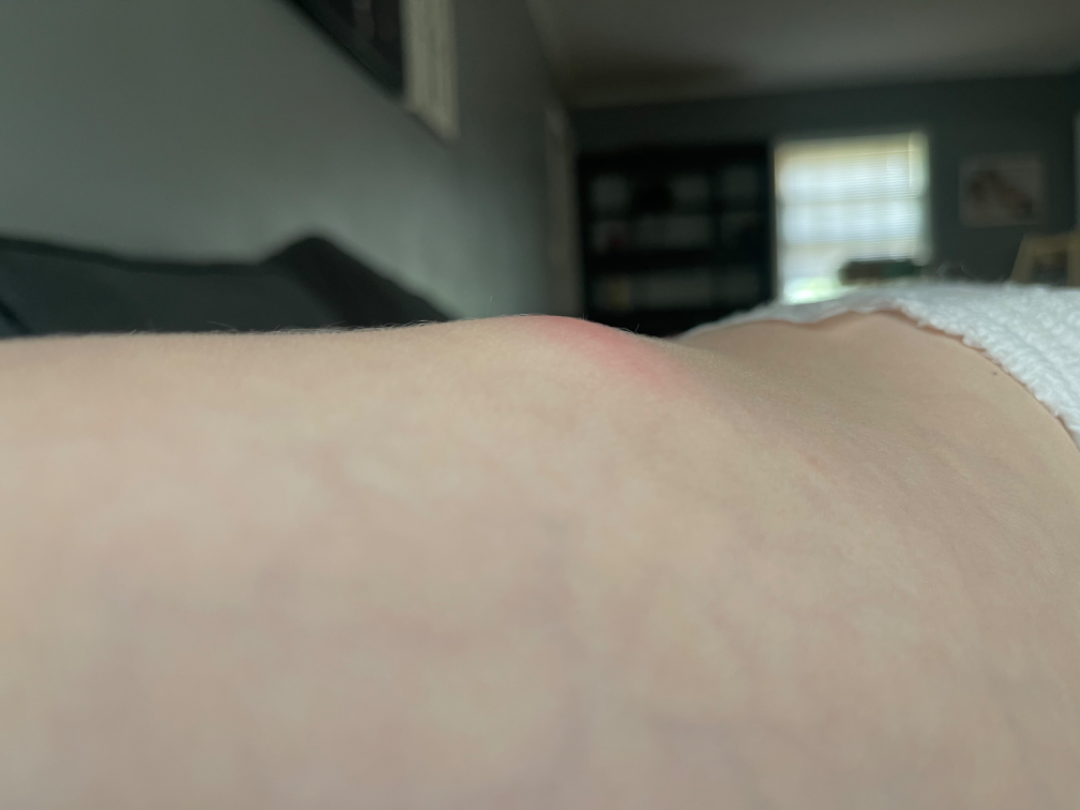Q: Could the case be diagnosed?
A: not assessable
Q: Where on the body?
A: back of the torso
Q: Image view?
A: at an angle